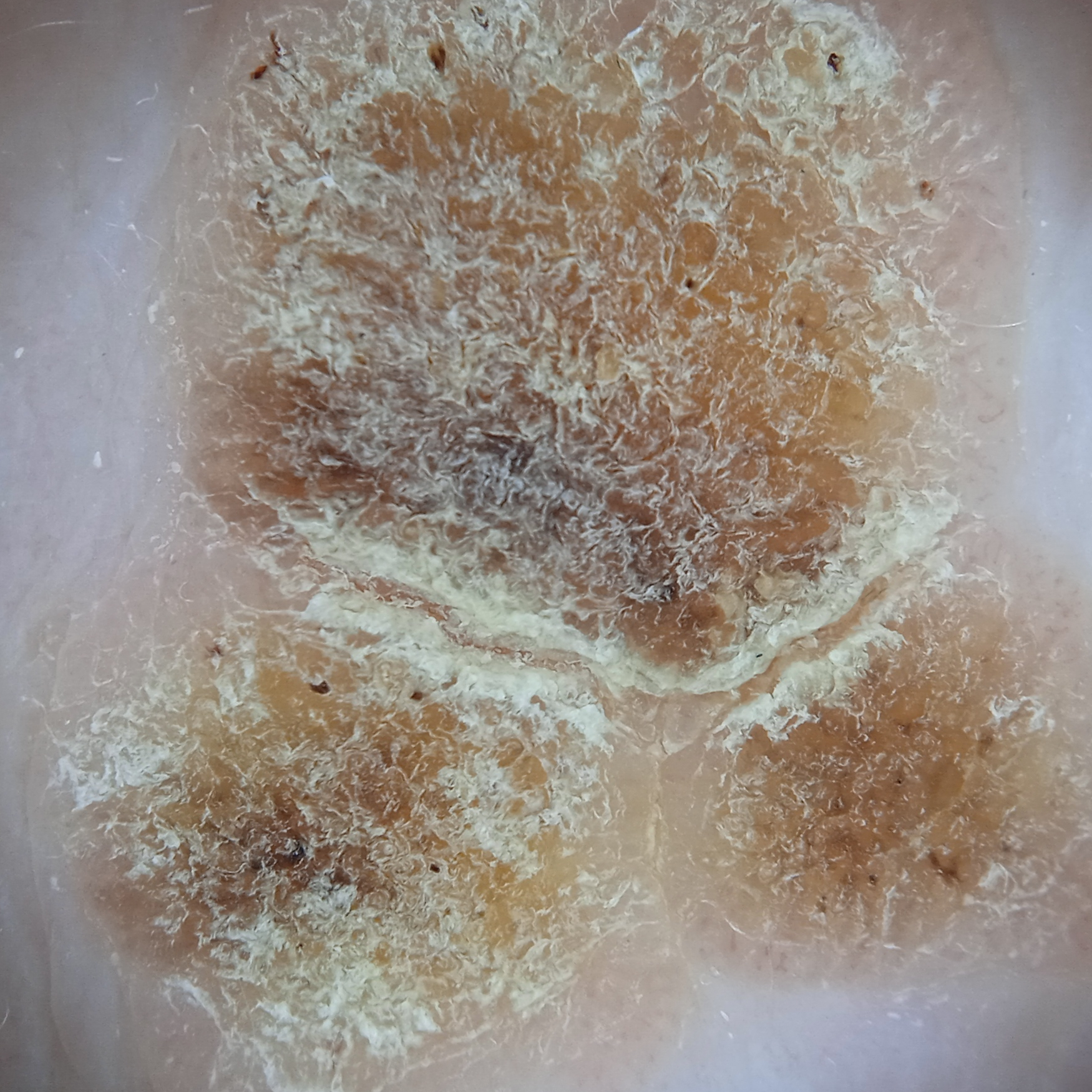The patient reports a personal history of cancer and a personal history of skin cancer. Collected as part of a research study, without a referral diagnosis. The patient describes having a moderate number of moles. A male patient 77 years of age. The patient says their skin reddens with sun exposure. The lesion involves the back. The lesion is about 14.2 mm across. Dermatologist review favored a seborrheic keratosis.